A clinical close-up of a skin lesion · a male patient age 76:
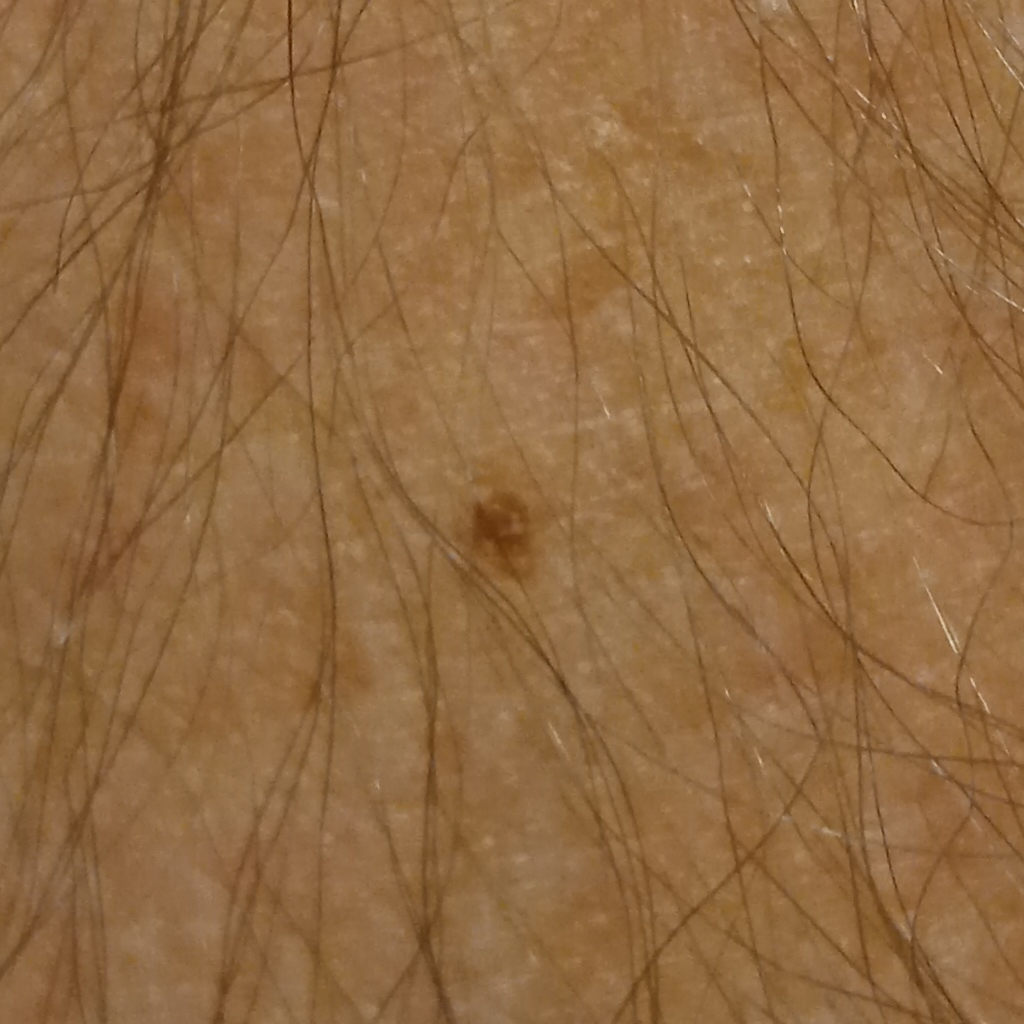location: an arm
size: 8.2 mm
assessment: melanocytic nevus (dermatologist consensus)